A dermoscopic image of a skin lesion: 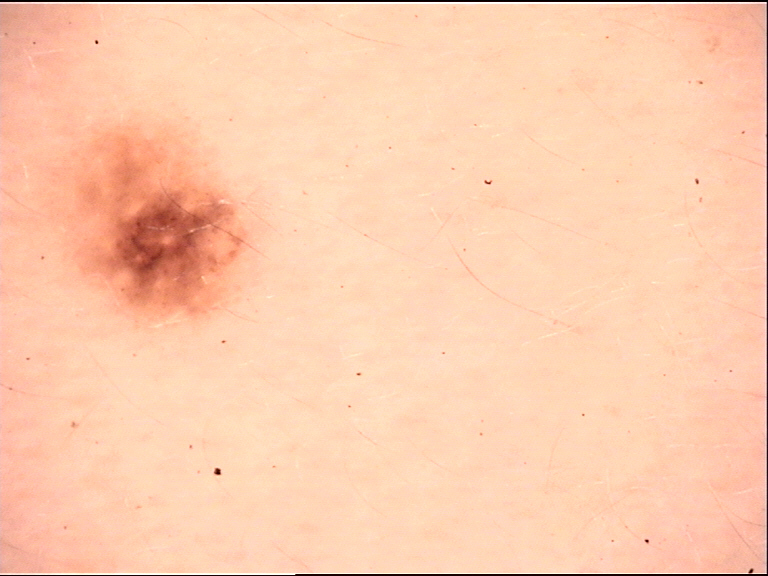- assessment: Miescher nevus (expert consensus)